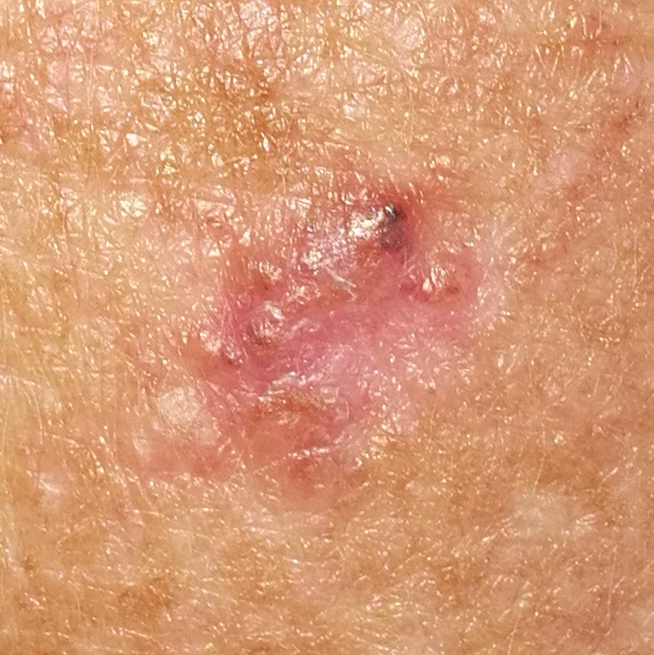Diagnosis:
Histopathology confirmed a basal cell carcinoma.